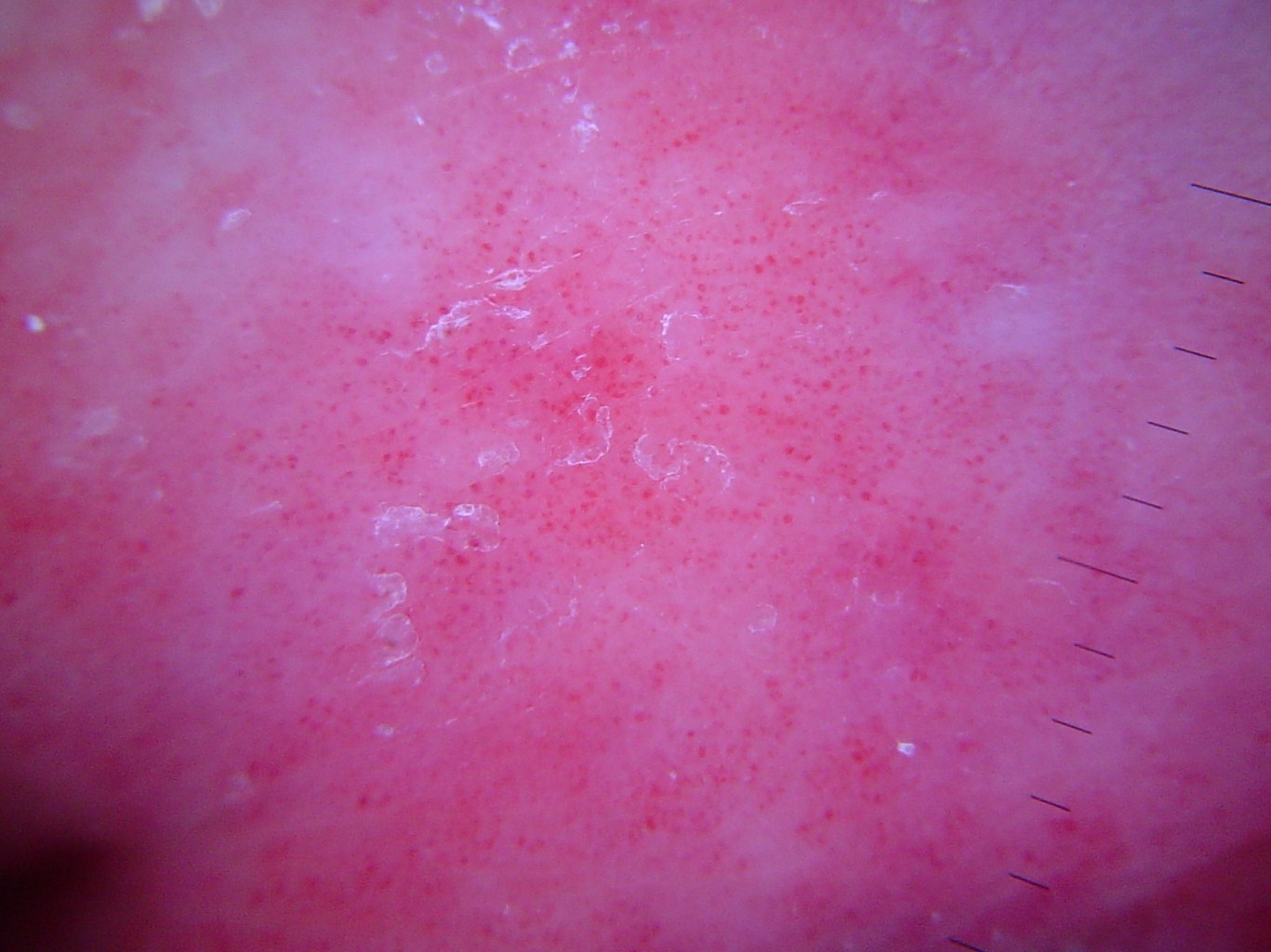{
  "diagnosis": {
    "name": "hemangioma",
    "code": "ha",
    "malignancy": "benign",
    "super_class": "non-melanocytic",
    "confirmation": "expert consensus"
  }
}